The photograph is a close-up of the affected area. The contributor is 60–69, male. The patient considered this a growth or mole. Located on the palm: 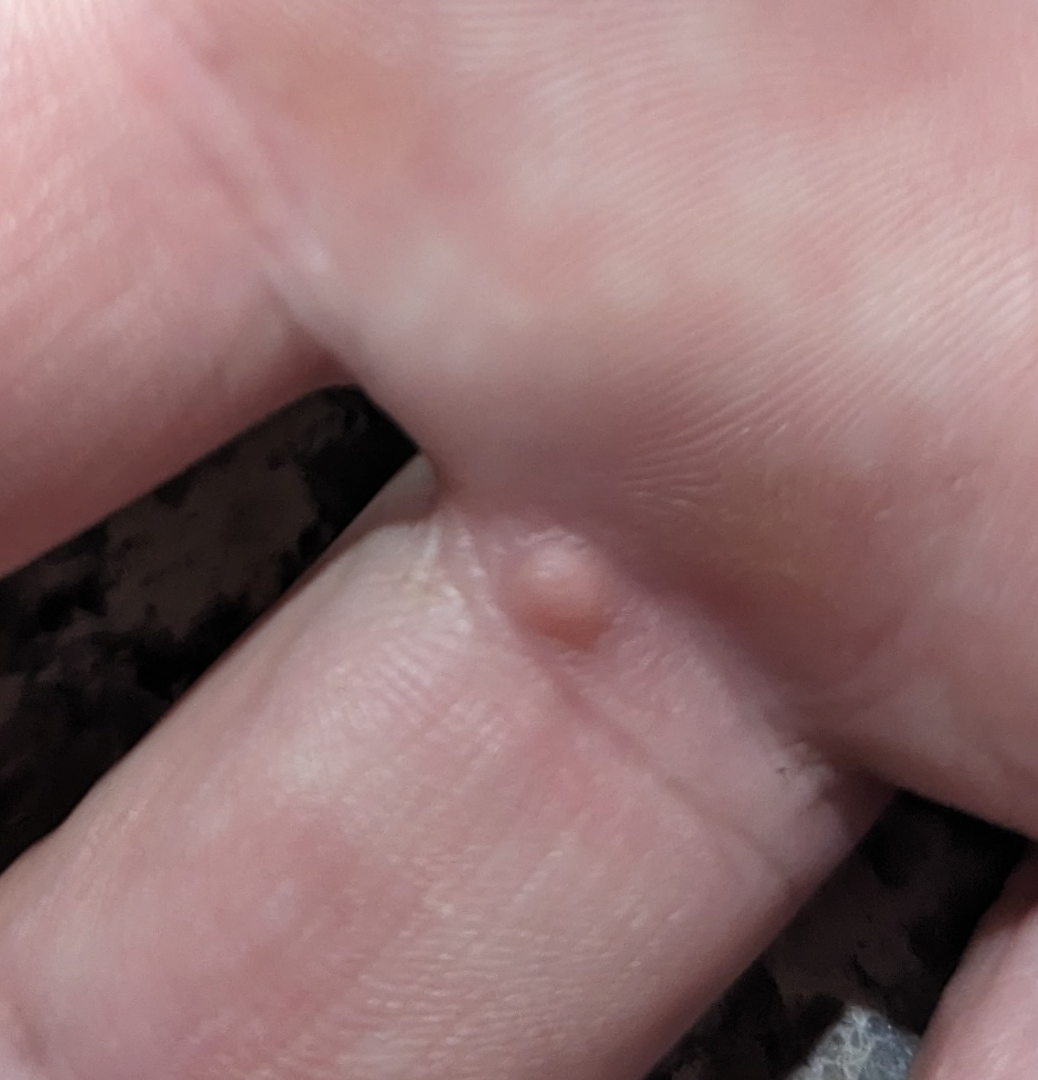Assessment: The leading consideration is Melanocytic Nevus; possibly Verruca vulgaris; less probable is Cyst; less likely is Adnexal neoplasm; a more distant consideration is Acquired digital fibrokeratoma.